The photo was captured at an angle; located on the head or neck, arm, back of the hand and leg:
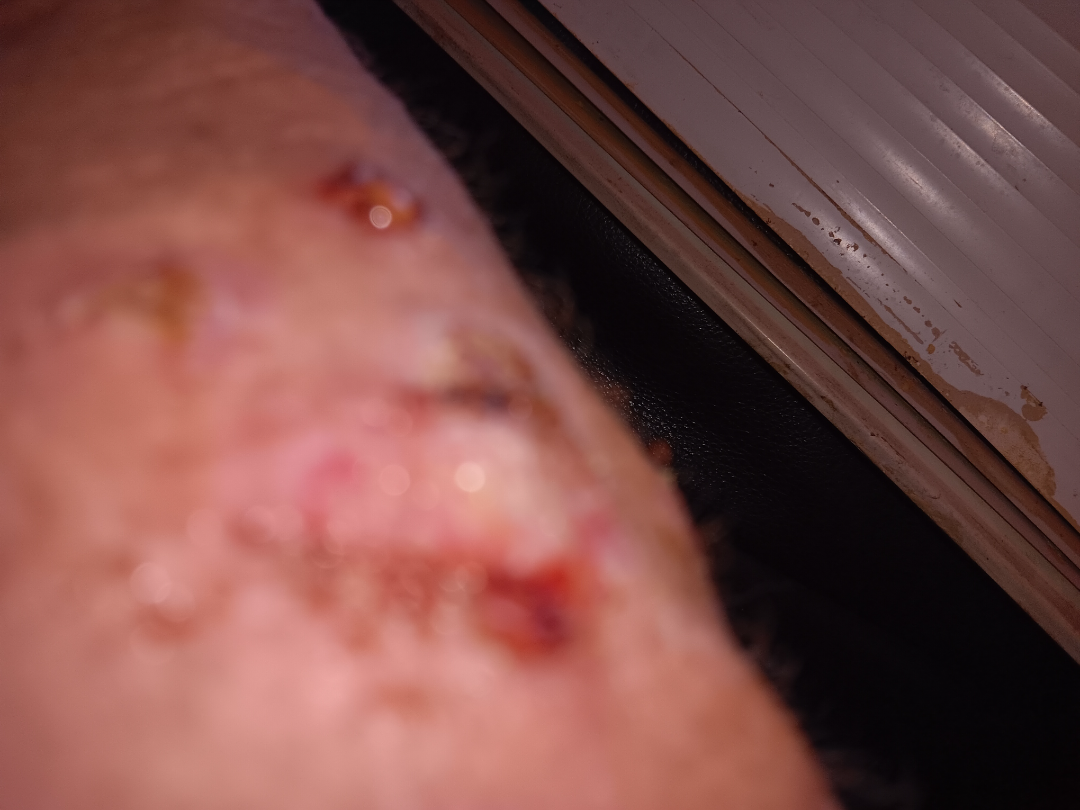| field | value |
|---|---|
| symptoms | itching, darkening, bothersome appearance, burning, enlargement, pain and bleeding |
| lesion texture | raised or bumpy, rough or flaky and fluid-filled |
| other reported symptoms | joint pain, shortness of breath, chills, fever and fatigue |
| patient's own categorization | a rash |
| differential | Abrasion, scrape, or scab and Ecthyma were each considered, in no particular order; possibly Impetigo; less likely is Mycetoma |